Recorded as FST II — 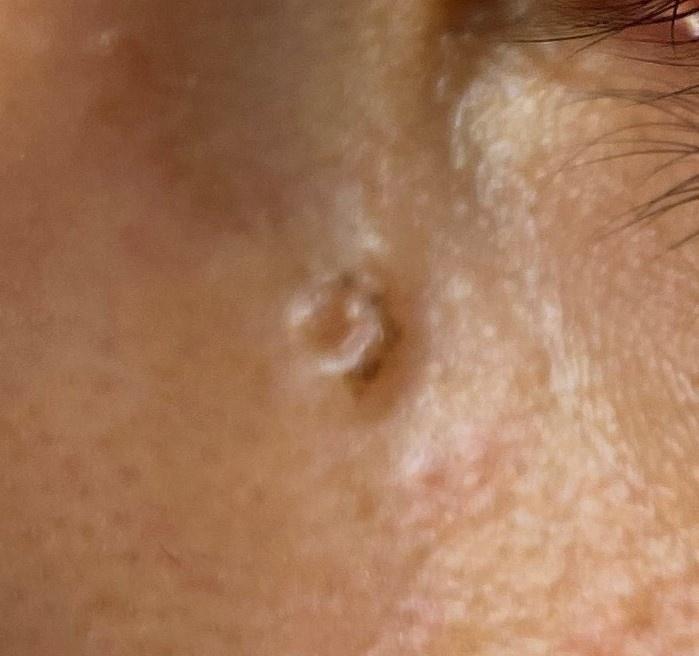| field | value |
|---|---|
| anatomic site | the head or neck |
| pathology | Basal cell carcinoma (biopsy-proven) |